A smartphone photograph of a skin lesion; a subject 54 years old.
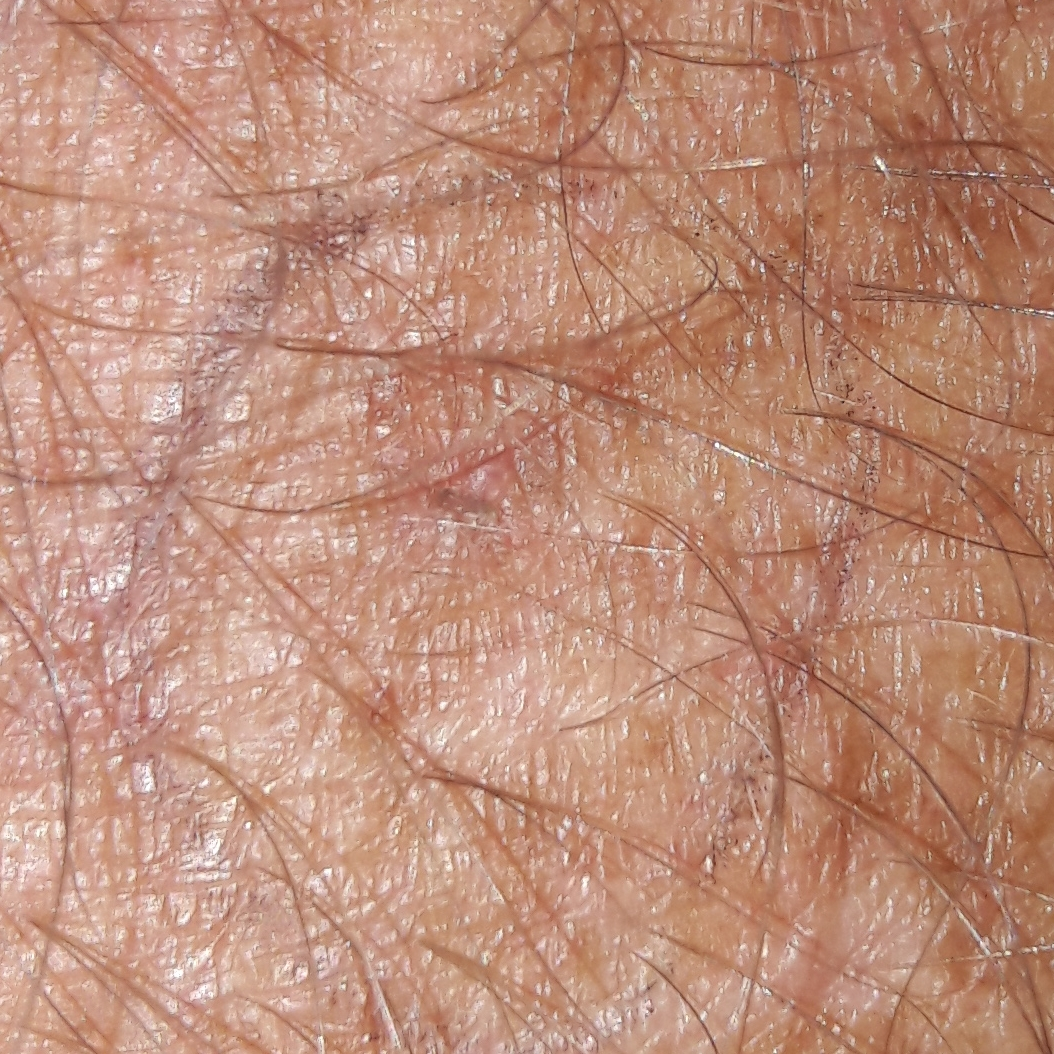region = a forearm
reported symptoms = itching / no elevation, no bleeding
diagnostic label = actinic keratosis (clinical consensus)